The patient described the issue as a rash; the condition has been present for less than one week; the lesion is described as raised or bumpy, rough or flaky and fluid-filled; symptoms reported: itching and bothersome appearance; this is a close-up image:
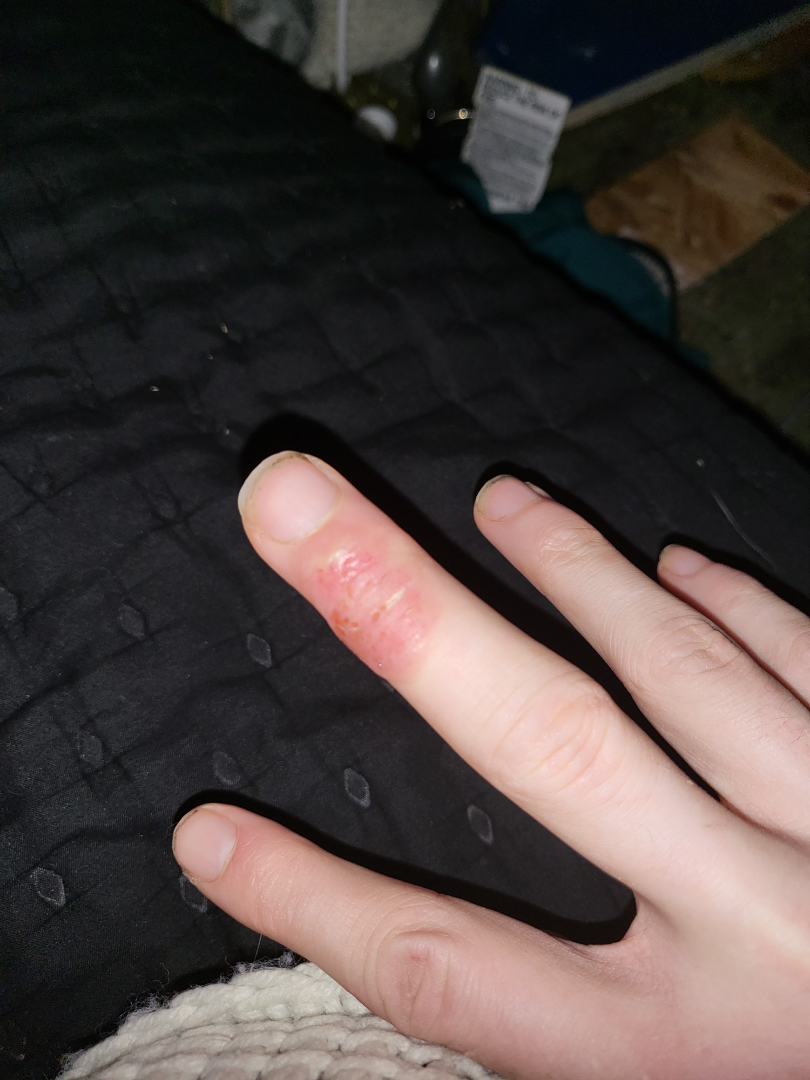| field | value |
|---|---|
| clinical impression | a single dermatologist reviewed the case: the leading consideration is Herpes Simplex; also on the differential is Skin and soft tissue atypical mycobacterial infection; less likely is Allergic Contact Dermatitis |